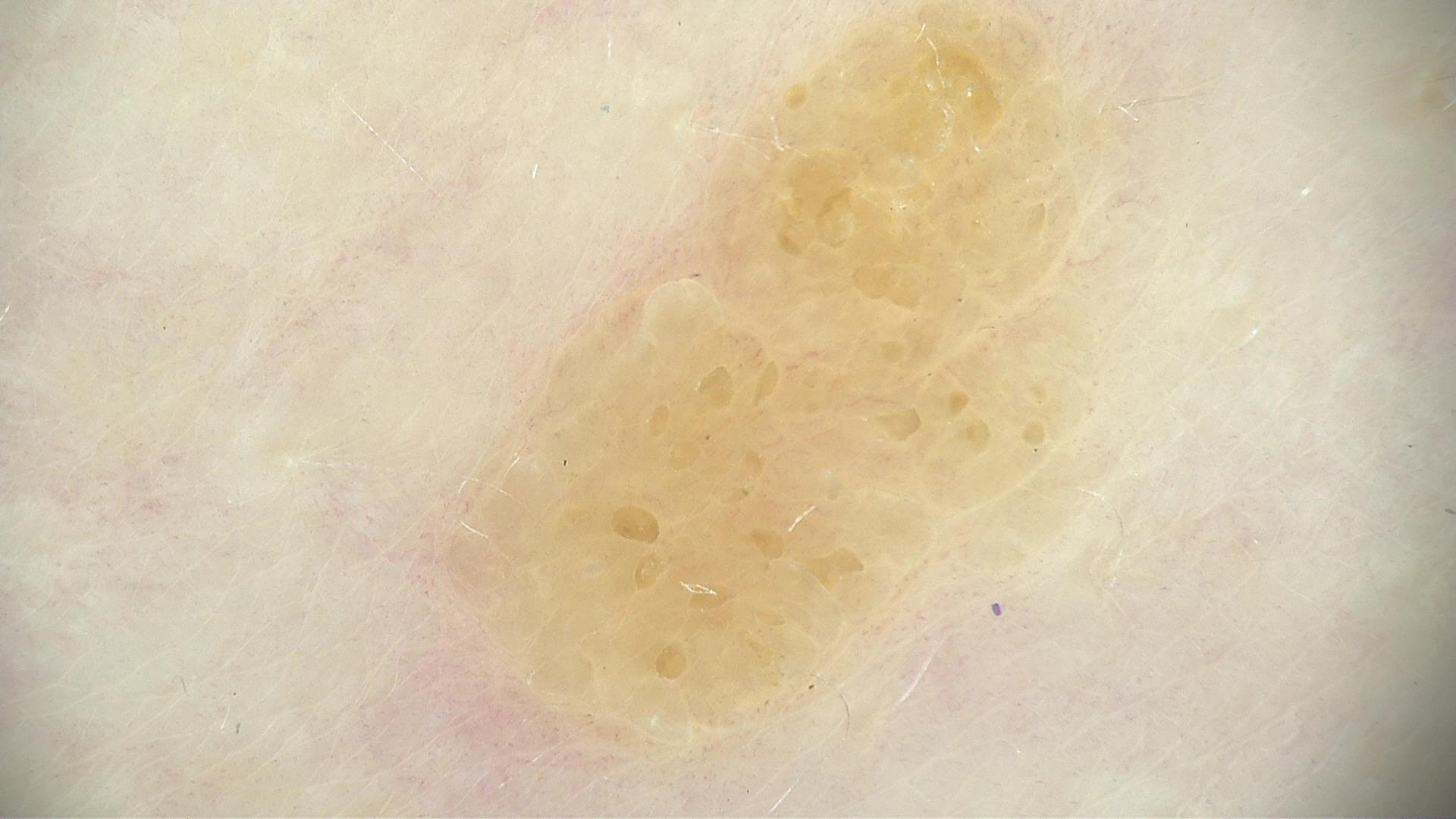Case:
– image type · dermoscopy
– lesion type · keratinocytic
– class · seborrheic keratosis (expert consensus)